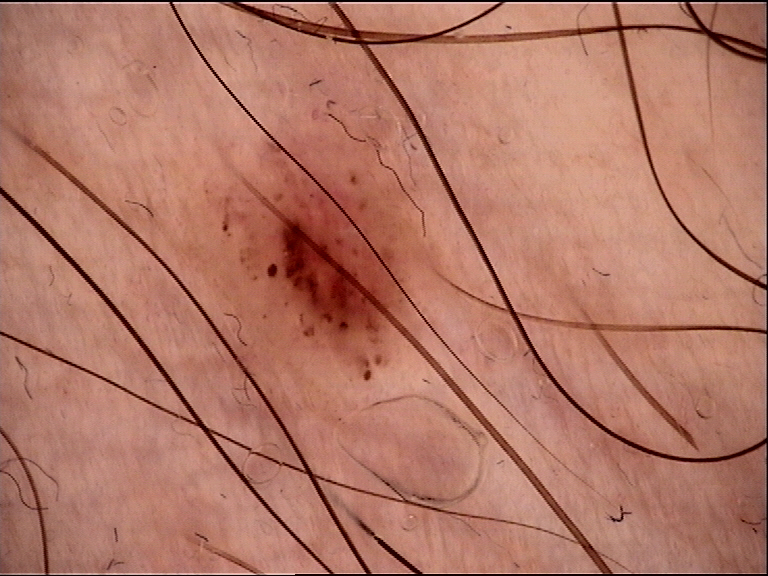<dermoscopy>
<diagnosis>
<name>dysplastic junctional nevus</name>
<code>jd</code>
<malignancy>benign</malignancy>
<super_class>melanocytic</super_class>
<confirmation>expert consensus</confirmation>
</diagnosis>
</dermoscopy>